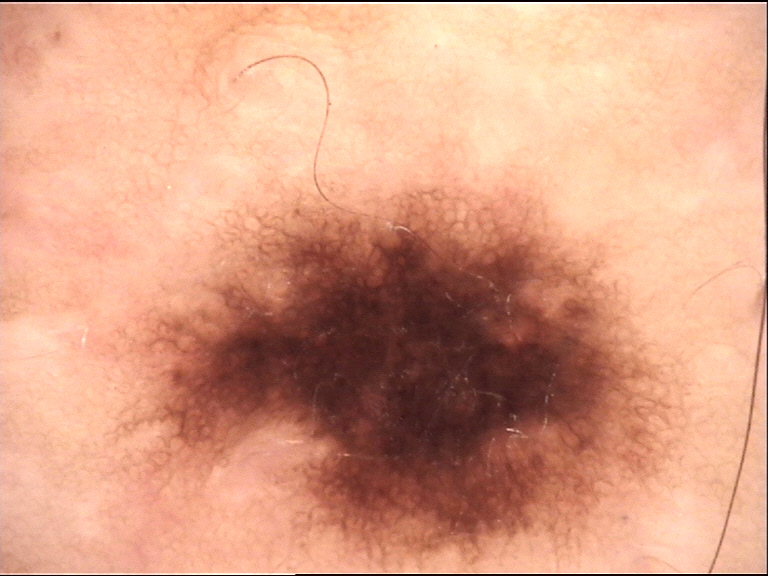class: dysplastic junctional nevus (expert consensus).